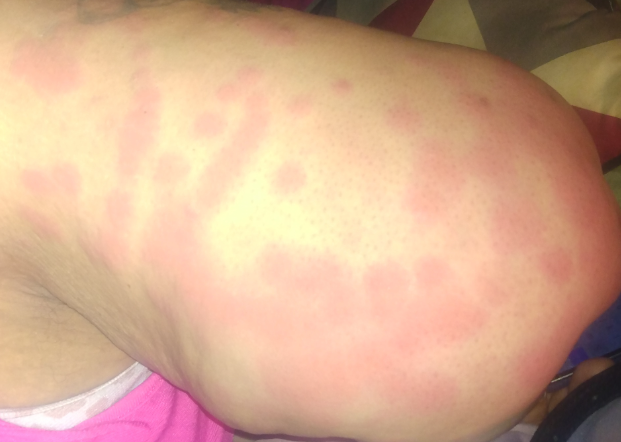The image was not sufficient for the reviewer to characterize the skin condition.
The contributor reports the condition has been present for less than one week.
Self-categorized by the patient as a rash.
The lesion involves the palm, back of the hand, head or neck and arm.
The lesion is described as raised or bumpy.
Female subject, age 40–49.
Skin tone: self-reported Fitzpatrick I.
This is a close-up image.